The back of the hand is involved, an image taken at an angle — 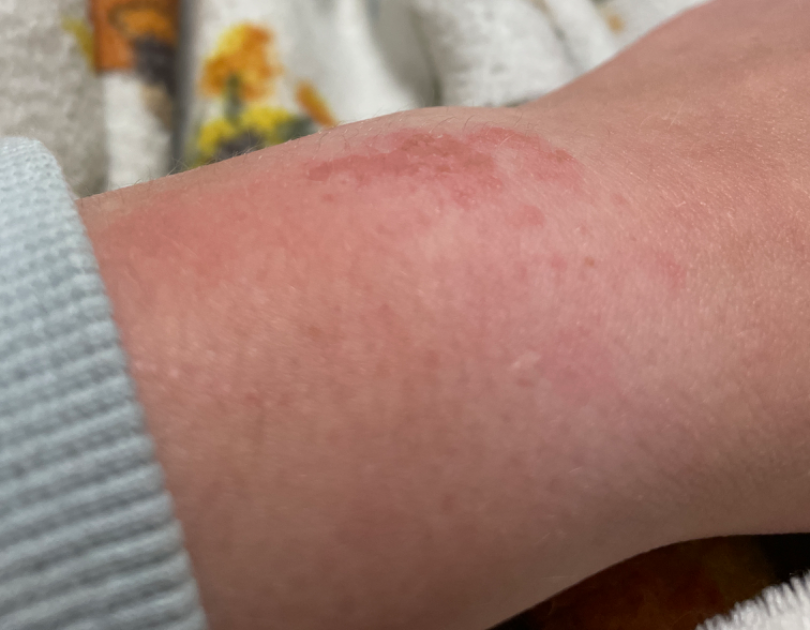Patient information:
Texture is reported as raised or bumpy. Symptoms reported: bothersome appearance, itching, enlargement and burning. Reported duration is less than one week. Self-categorized by the patient as a rash. Skin tone: Fitzpatrick III. No associated systemic symptoms reported.
Review:
On dermatologist assessment of the image: in keeping with Allergic Contact Dermatitis.